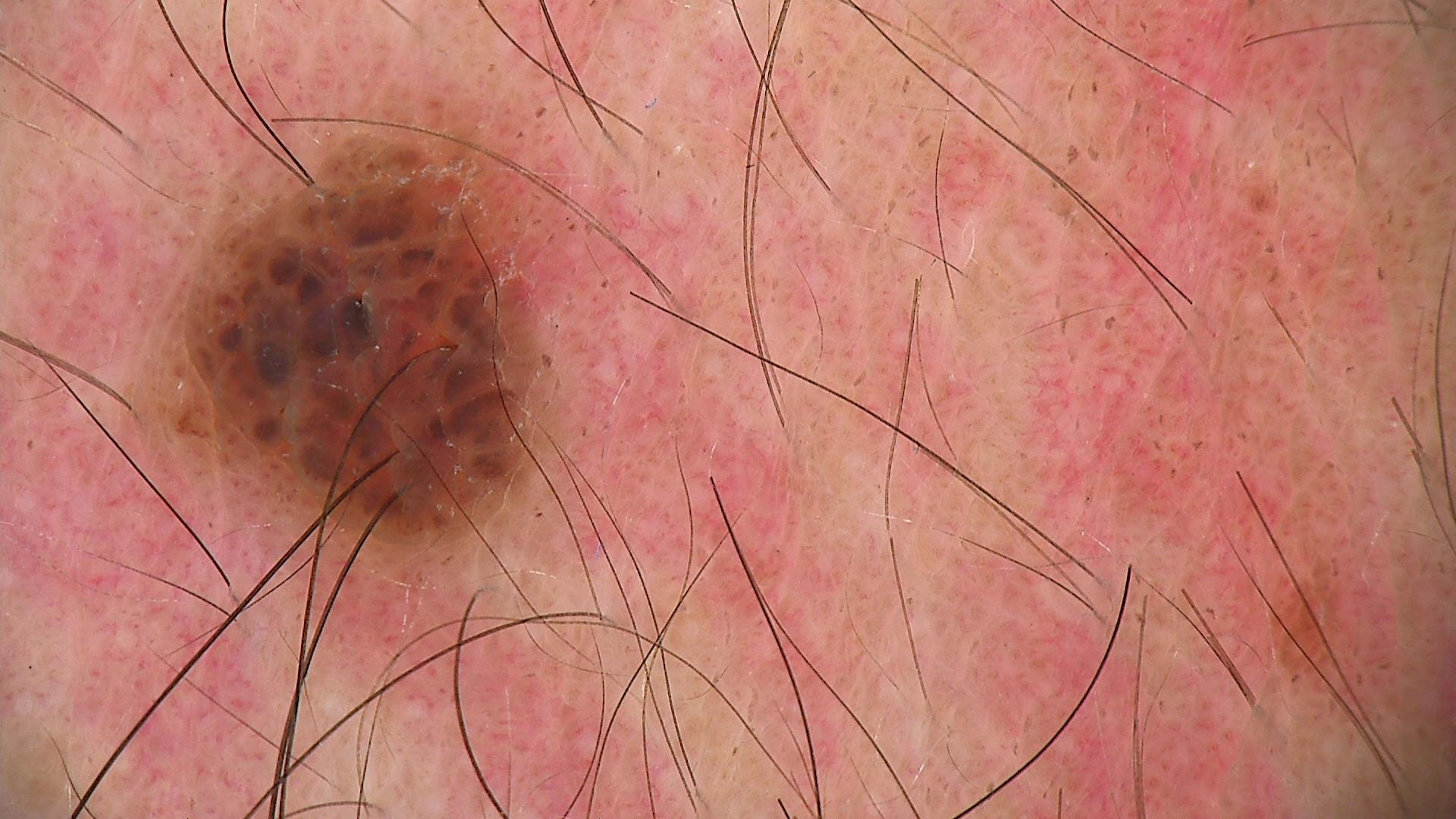Labeled as a compound nevus.